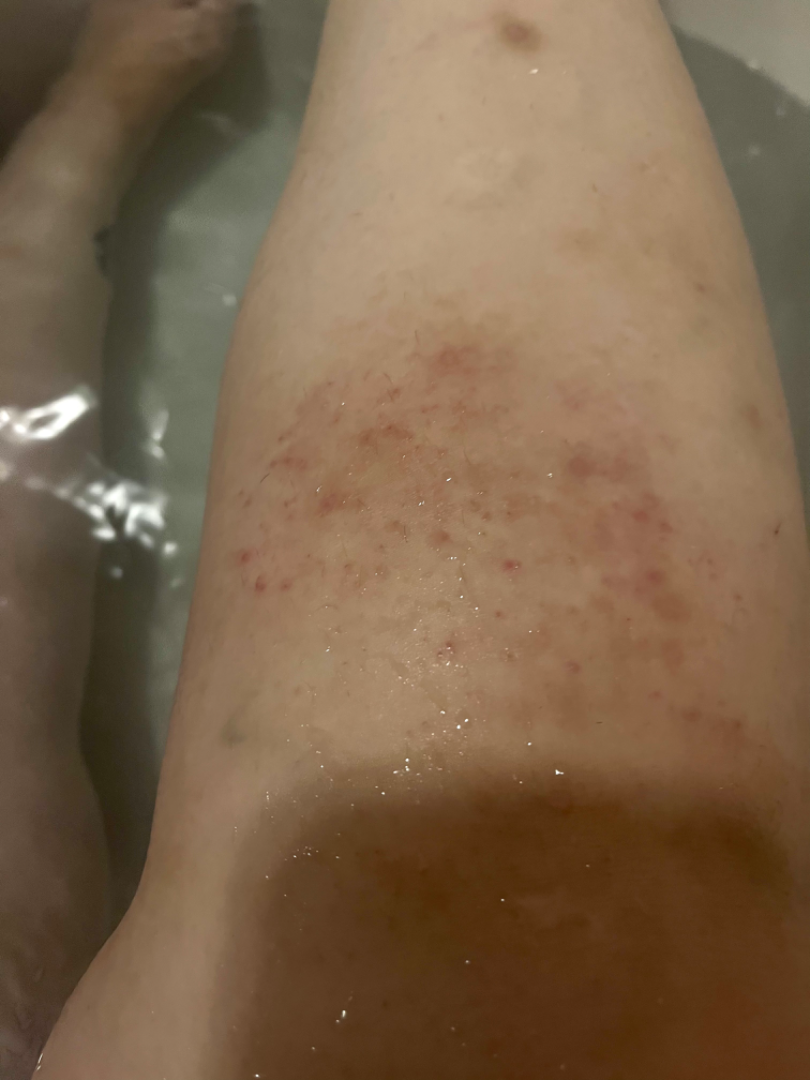Q: Duration?
A: one to three months
Q: Age and sex?
A: female
Q: Constitutional symptoms?
A: fatigue
Q: Image view?
A: close-up
Q: Fitzpatrick or Monk tone?
A: Fitzpatrick phototype III; human graders estimated Monk Skin Tone 3
Q: How does the patient describe it?
A: a rash
Q: Anatomic location?
A: back of the torso
Q: What conditions are considered?
A: favoring Pigmented purpuric eruption; also consider Eczema